A dermoscopy image of a single skin lesion.
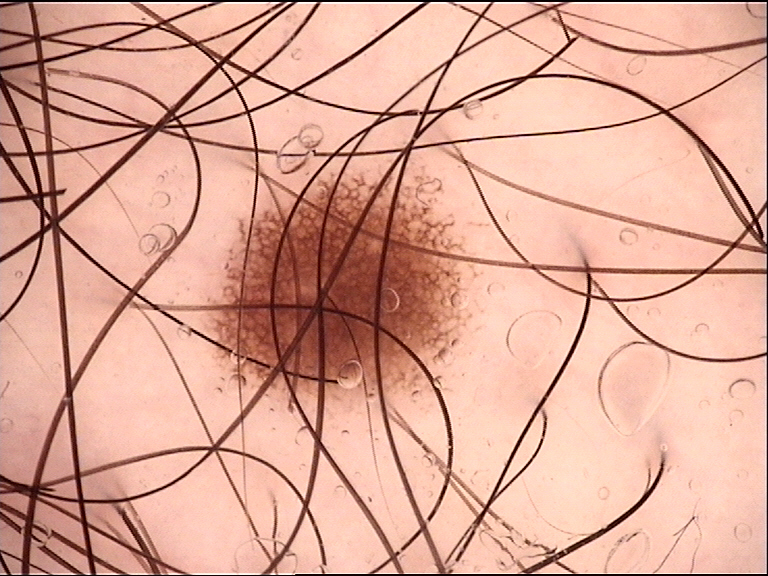diagnostic label: dysplastic junctional nevus (expert consensus)